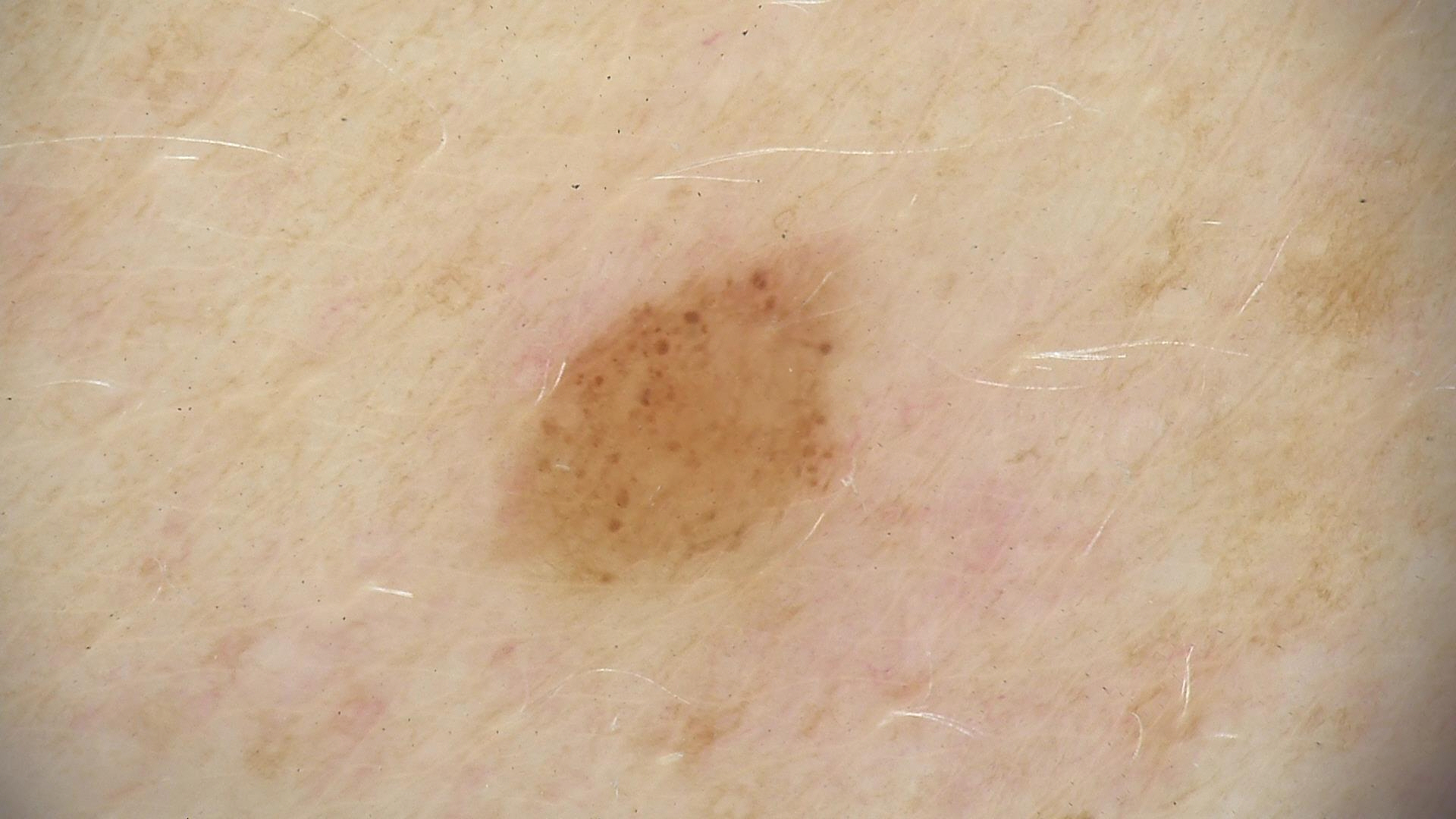Q: What is the diagnosis?
A: dysplastic junctional nevus (expert consensus)